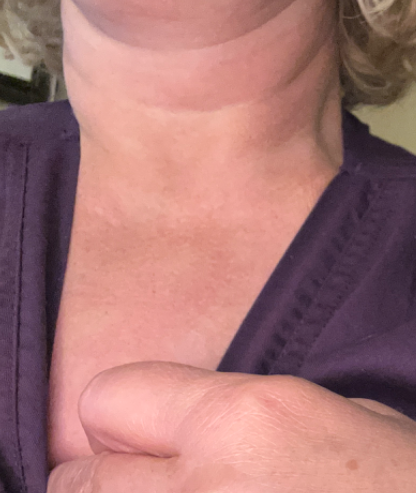Findings: No skin condition was discernible on photographic review.